A dermoscopy image of a skin lesion · the patient reports a personal history of cancer · the patient describes having a moderate number of moles · the patient says their skin tans without first burning · a male subject age 65 · imaged for a research study, with no referral diagnosis recorded.
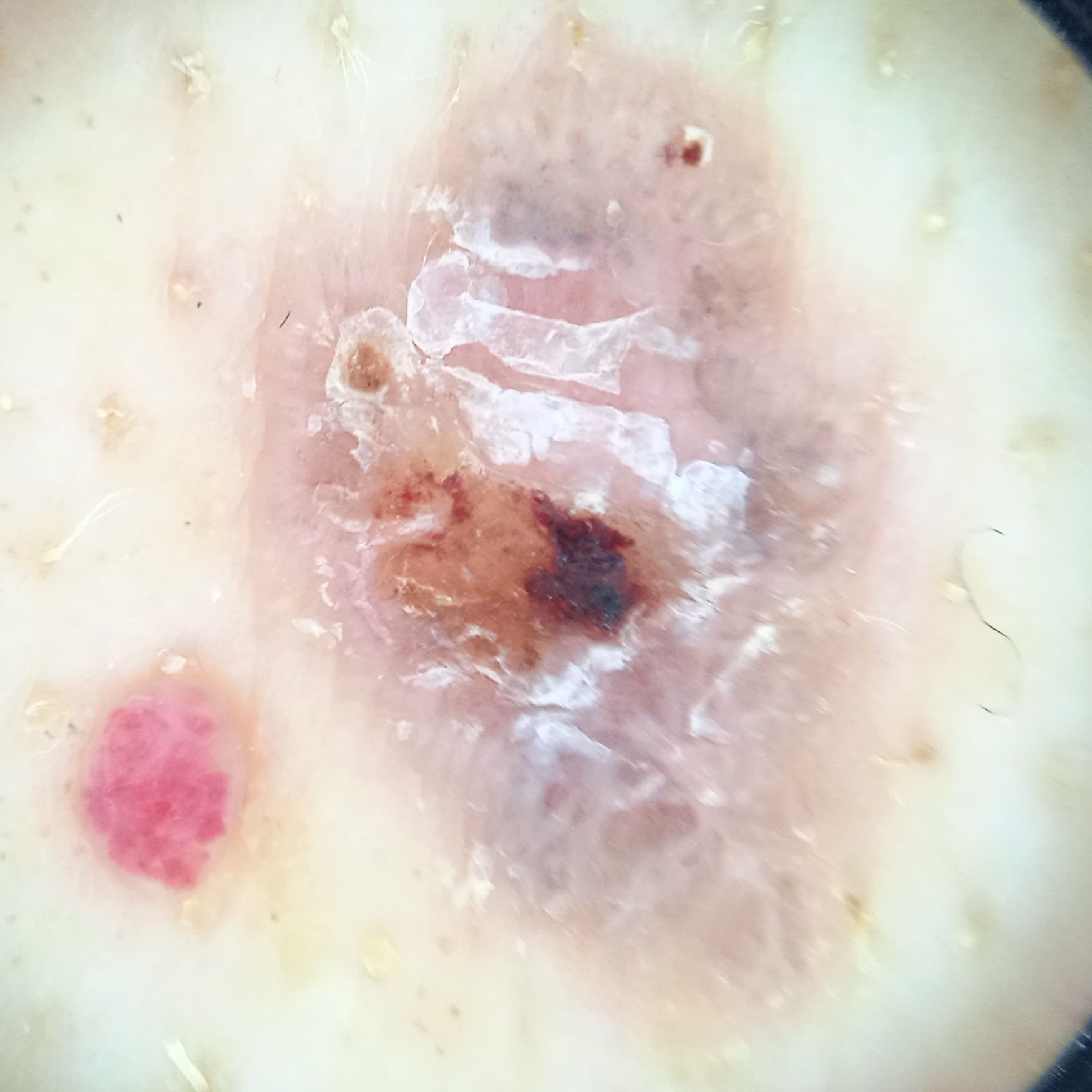The lesion measures approximately 11.9 mm. On independent review by four dermatologists, the agreed diagnosis was a basal cell carcinoma; the reviewers' opinions were divided; the reviewers were moderately confident.